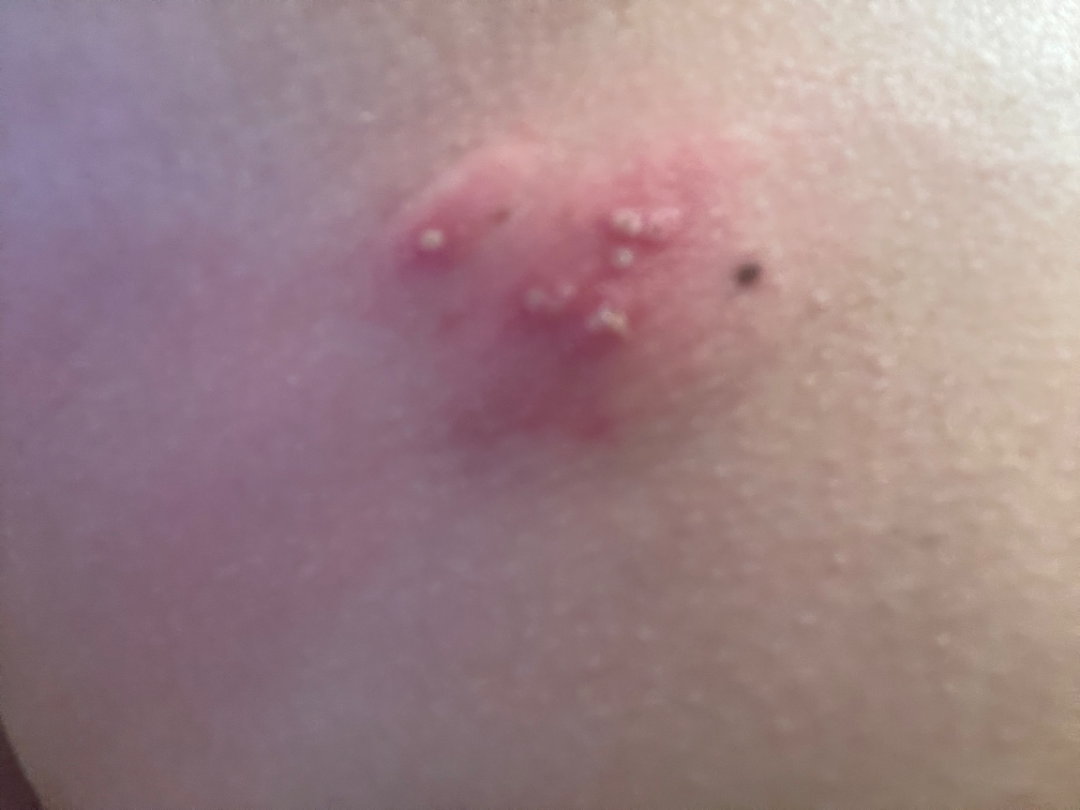The image was not sufficient for the reviewer to characterize the skin condition. The lesion involves the leg. The patient notes burning. The lesion is described as raised or bumpy. No constitutional symptoms were reported. The condition has been present for about one day. Self-categorized by the patient as a rash. This is a close-up image.